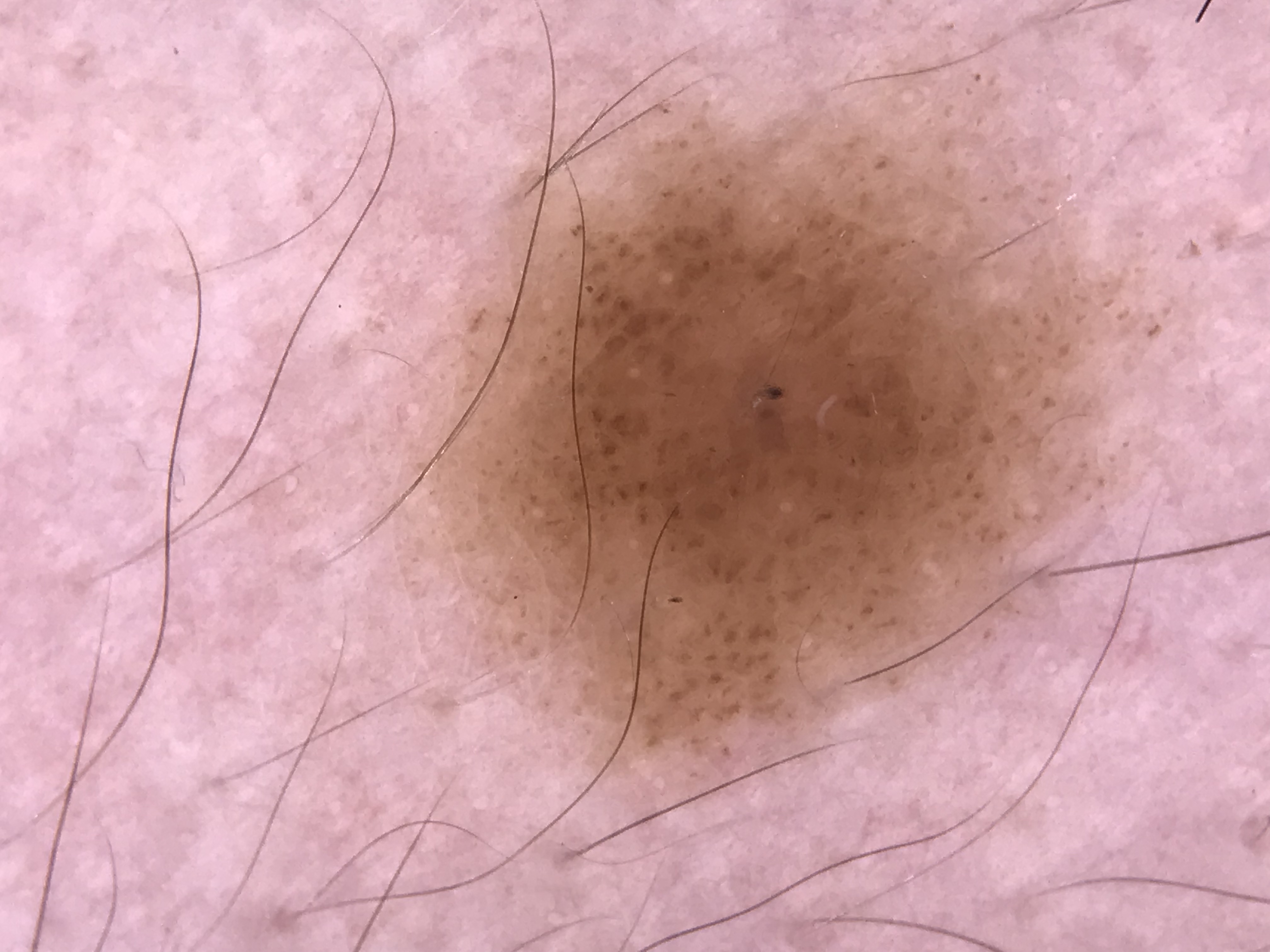This is a banal lesion. Classified as a compound nevus.